A skin lesion imaged with a dermatoscope; a male patient approximately 70 years of age: 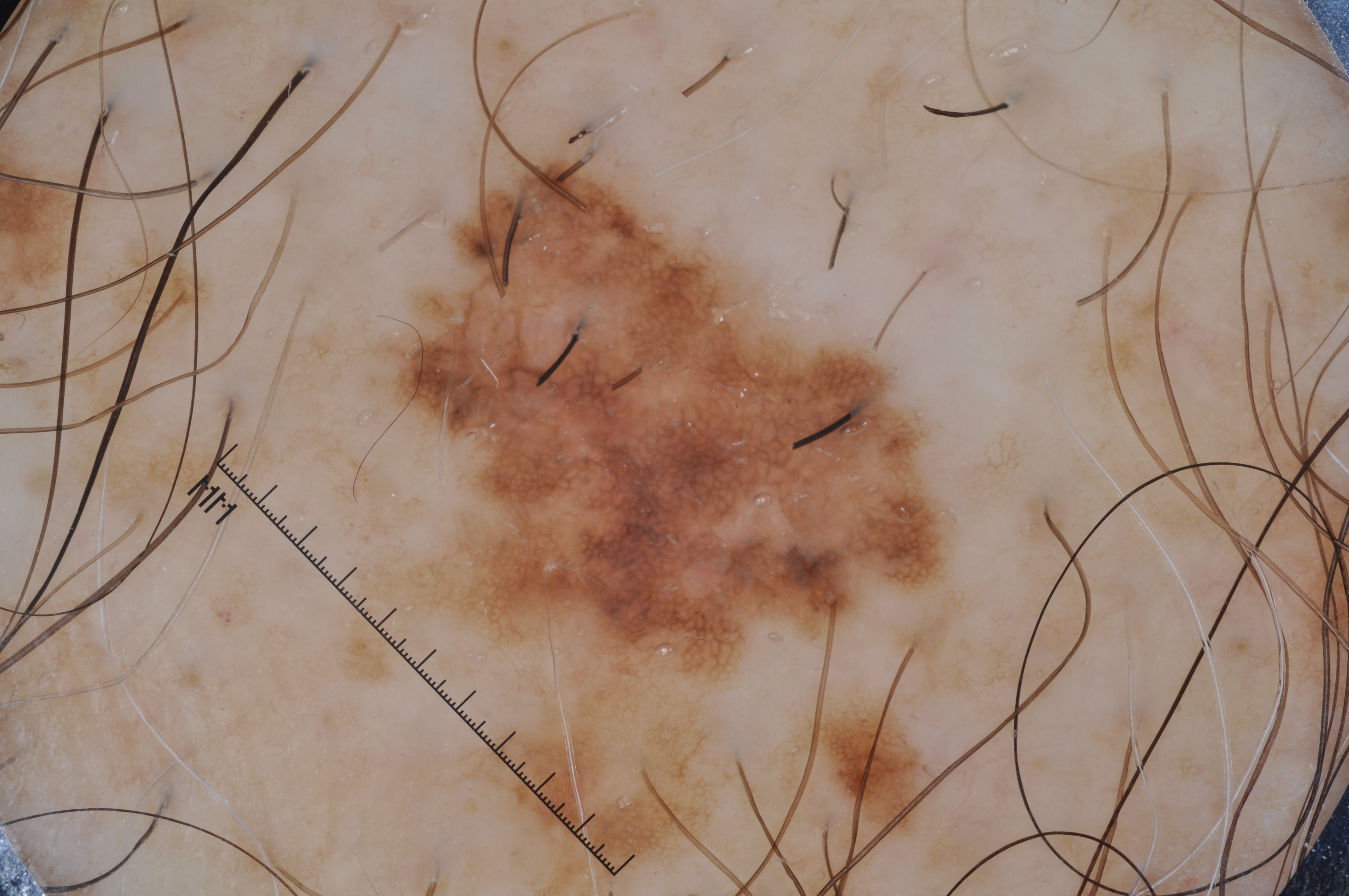The lesion covers approximately 35% of the dermoscopic field. Dermoscopy demonstrates milia-like cysts and pigment network; no streaks or negative network. The lesion's extent is x1=265, y1=150, x2=993, y2=894. Histopathologically confirmed as a melanoma, a skin cancer.